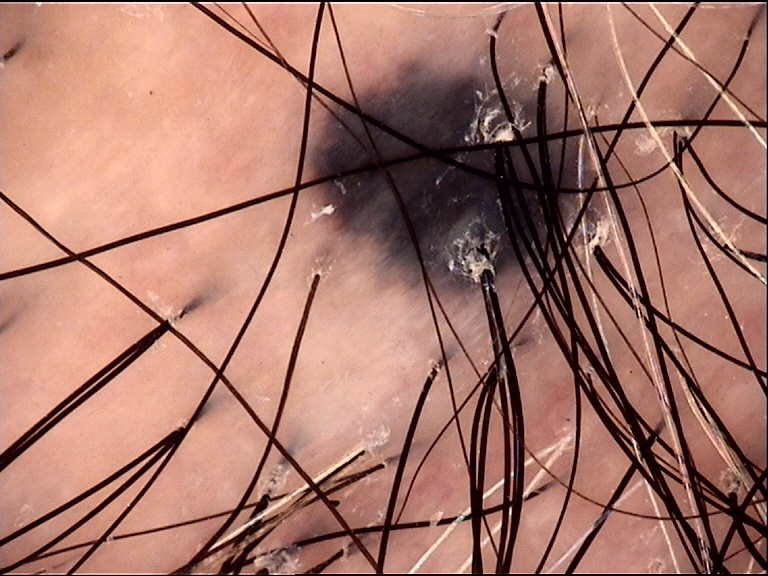| feature | finding |
|---|---|
| diagnosis | blue nevus (expert consensus) |